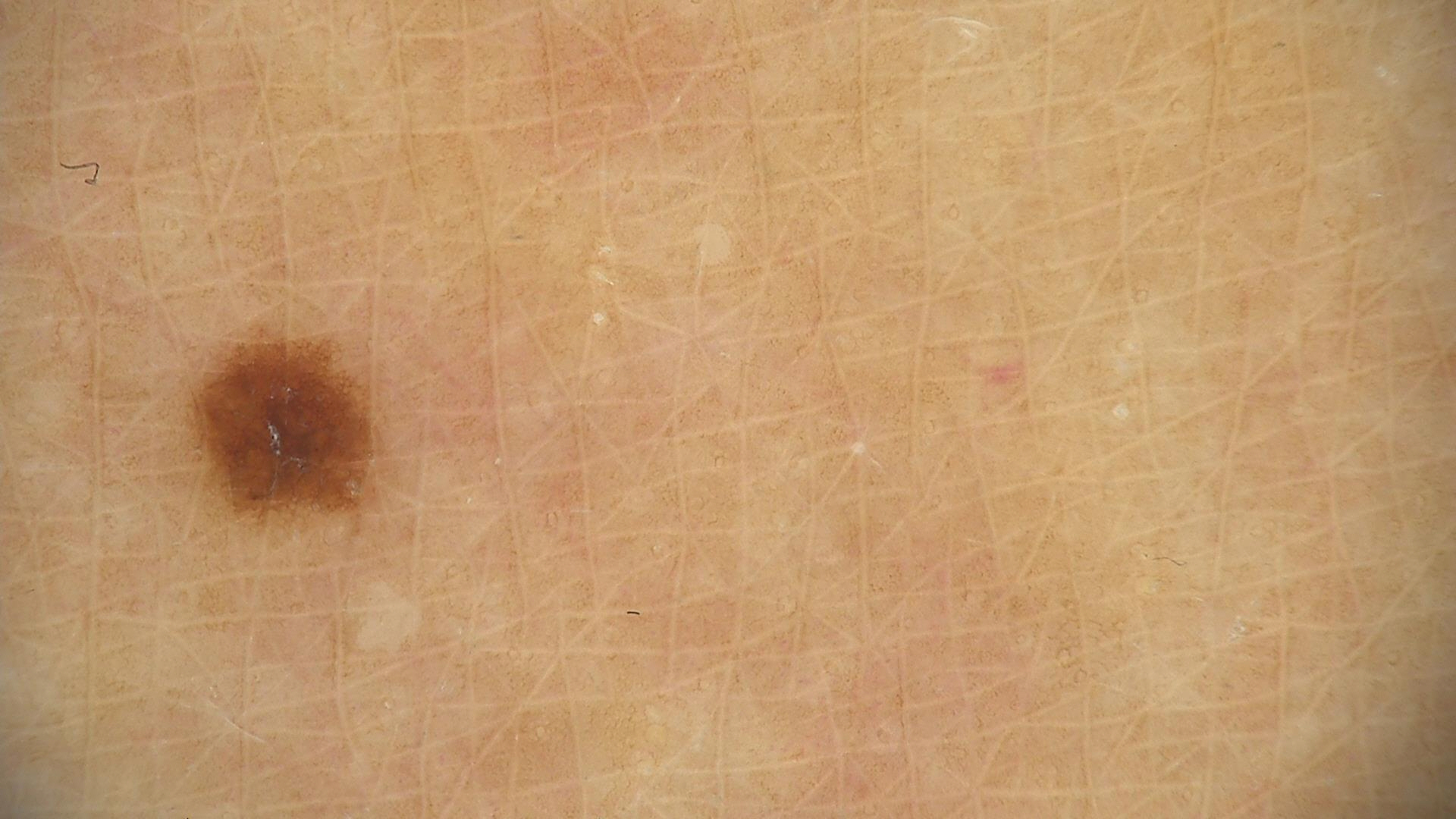Summary: A dermoscopic image of a skin lesion. Conclusion: The diagnostic label was a banal lesion — a junctional nevus.